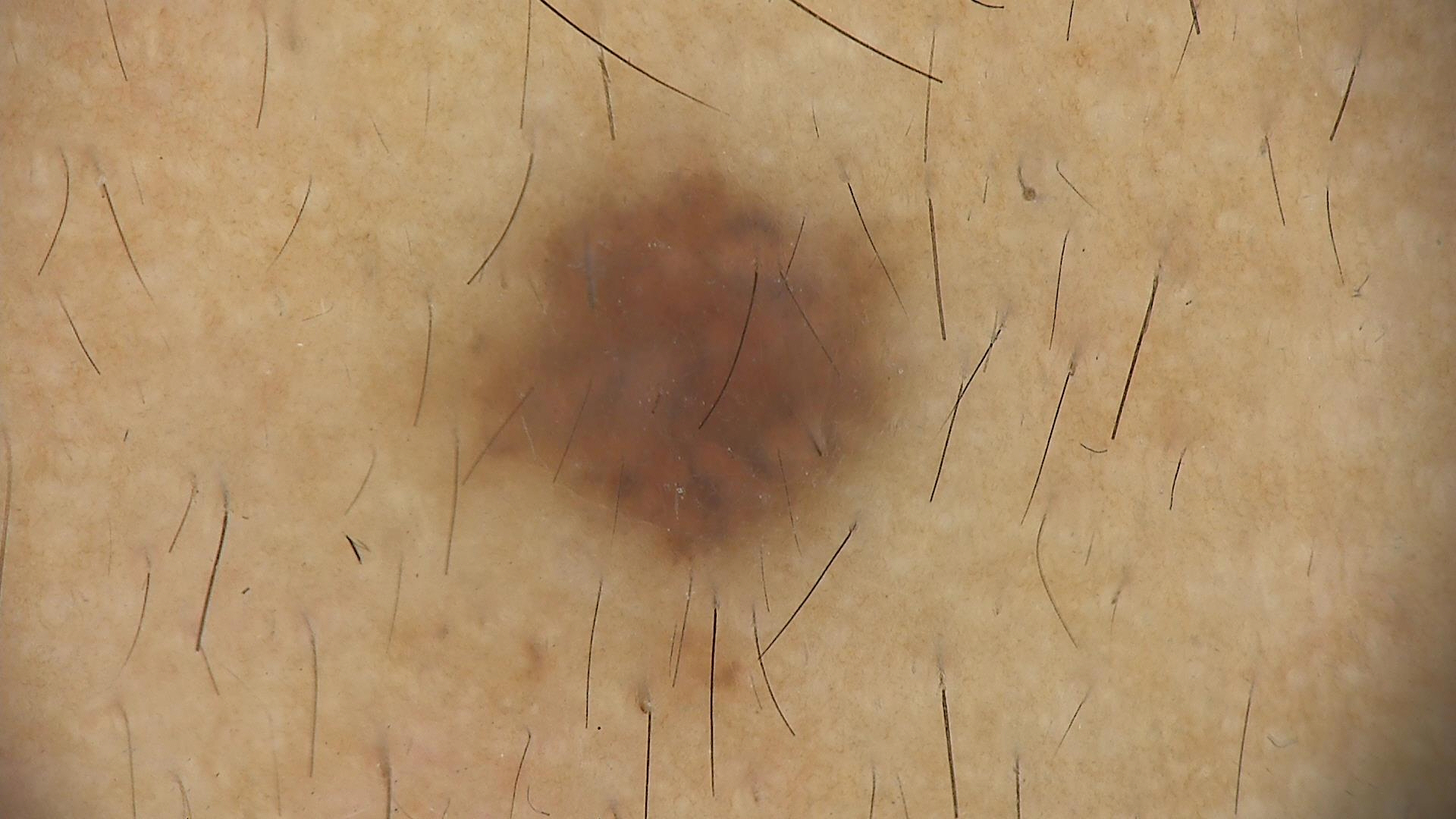imaging: dermoscopy | assessment: dysplastic compound nevus (expert consensus).